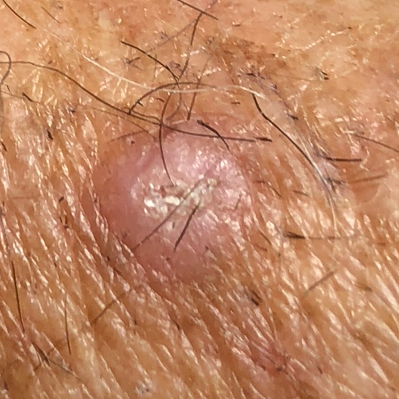patient:
  age: 74
  gender: male
skin_type: II
risk_factors:
  positive:
    - prior cancer (patient or family)
    - prior skin cancer (patient or family)
    - pesticide exposure
  negative:
    - smoking
    - alcohol use
image: clinical photograph
lesion_location: a forearm
lesion_size:
  diameter_1_mm: 7.0
  diameter_2_mm: 5.0
symptoms:
  present:
    - elevation
diagnosis:
  name: actinic keratosis
  code: ACK
  malignancy: indeterminate
  confirmation: histopathology